A male subject, aged 13 to 17; this is a dermoscopic photograph of a skin lesion: 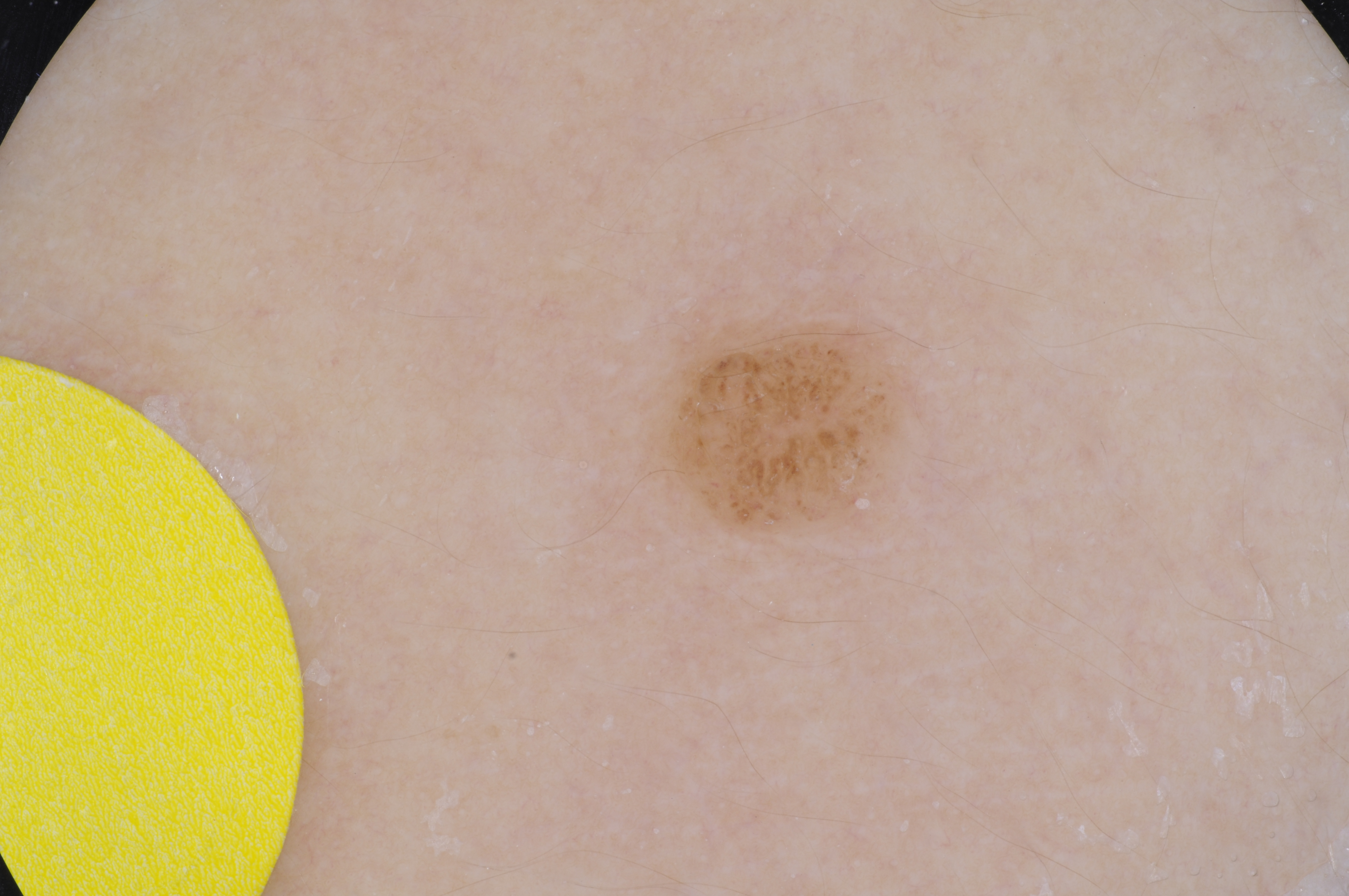<record>
<lesion_location>
  <bbox_xyxy>655, 318, 920, 540</bbox_xyxy>
</lesion_location>
<lesion_extent>small</lesion_extent>
<dermoscopic_features>
  <present/>
  <absent>milia-like cysts, streaks, globules, negative network, pigment network</absent>
</dermoscopic_features>
<diagnosis>
  <name>melanocytic nevus</name>
  <malignancy>benign</malignancy>
  <lineage>melanocytic</lineage>
  <provenance>clinical</provenance>
</diagnosis>
</record>